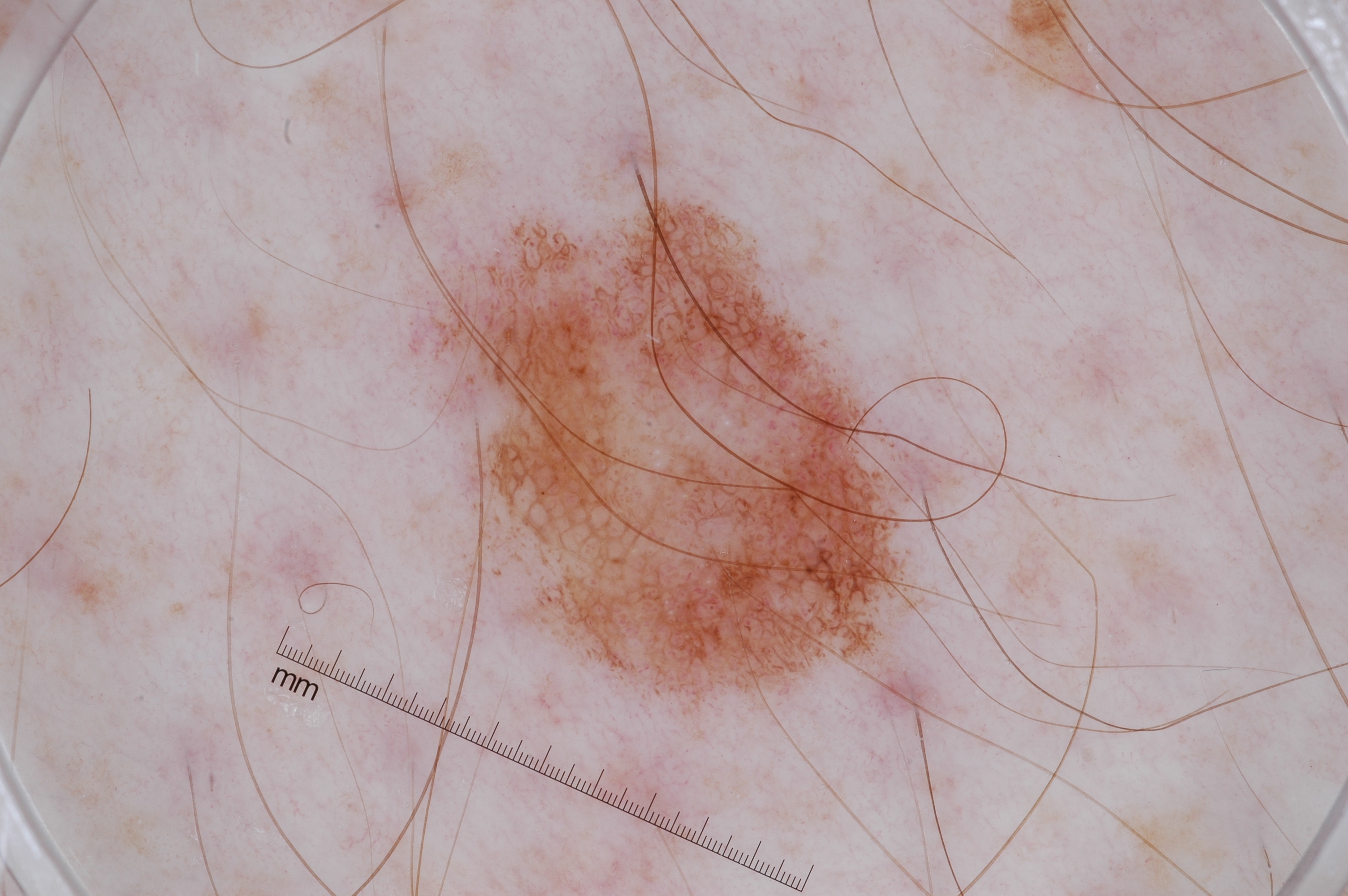Findings:
• image type: dermoscopy
• dermoscopic findings: pigment network, milia-like cysts, and globules
• lesion size: ~17% of the field
• lesion location: [431,186,954,729]
• assessment: a melanocytic nevus, a benign lesion